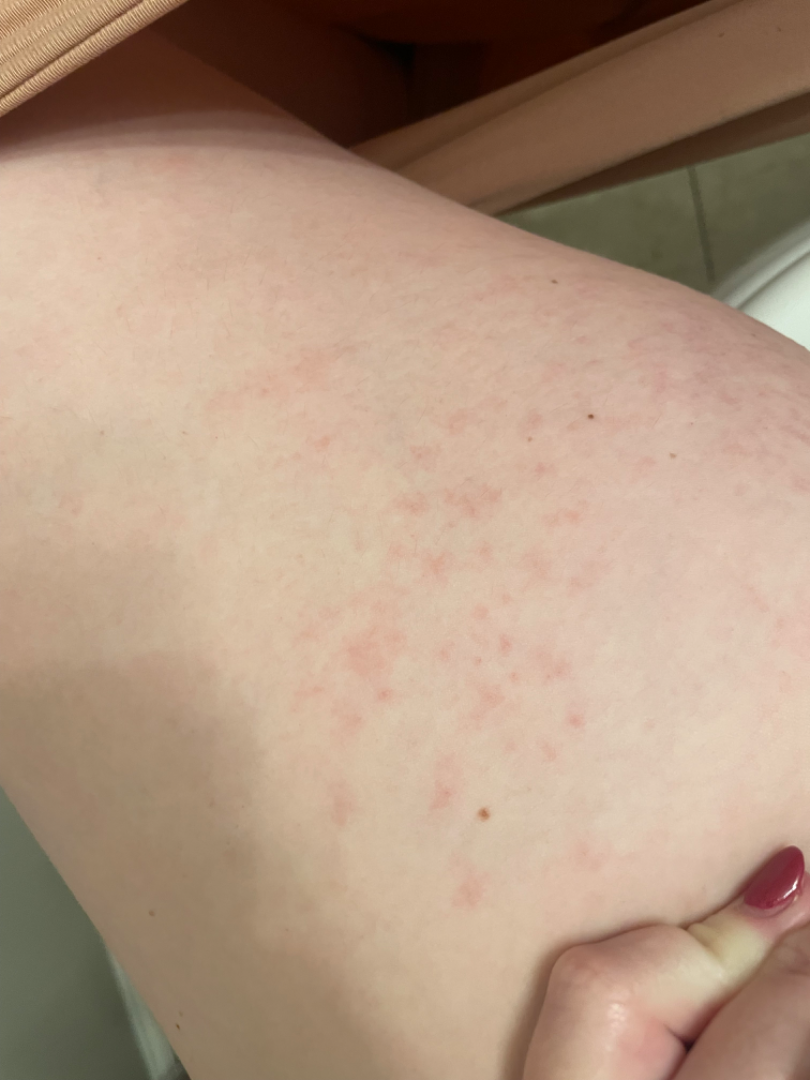Background:
The lesion is associated with itching. The affected area is the arm and leg. No constitutional symptoms were reported. Self-categorized by the patient as a rash. The lesion is described as raised or bumpy. Close-up view. The condition has been present for less than one week. The patient is a female aged 18–29.
Findings:
On remote dermatologist review, Eczema and Allergic Contact Dermatitis were each considered, in no particular order; also consider Drug Rash.